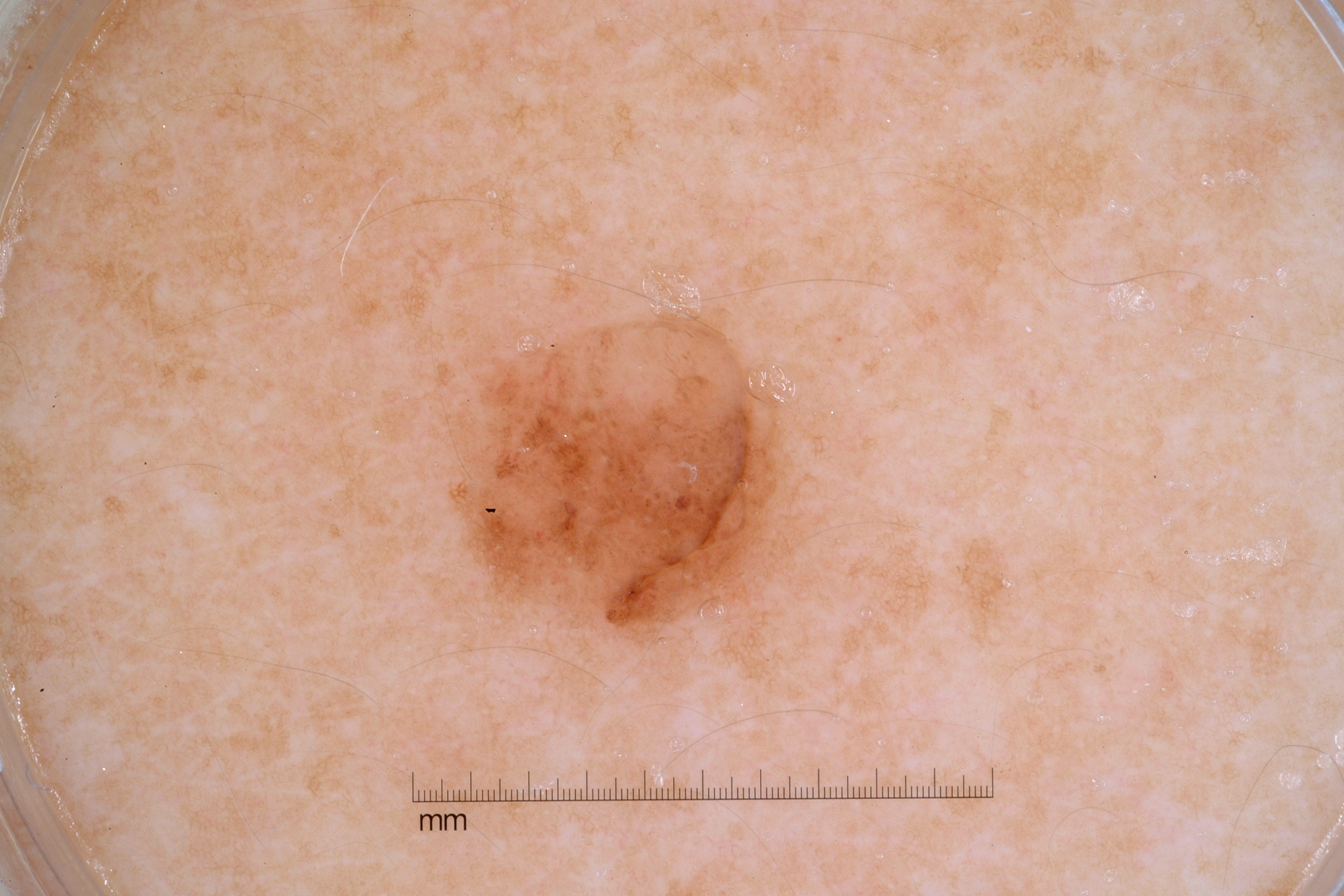This is a dermoscopic photograph of a skin lesion. In (x1, y1, x2, y2) order, the visible lesion spans bbox=[462, 322, 787, 637]. On dermoscopy, the lesion shows pigment network and milia-like cysts; no negative network or streaks. A small lesion occupying a minor part of the field. The clinical diagnosis was a melanocytic nevus, a benign skin lesion.